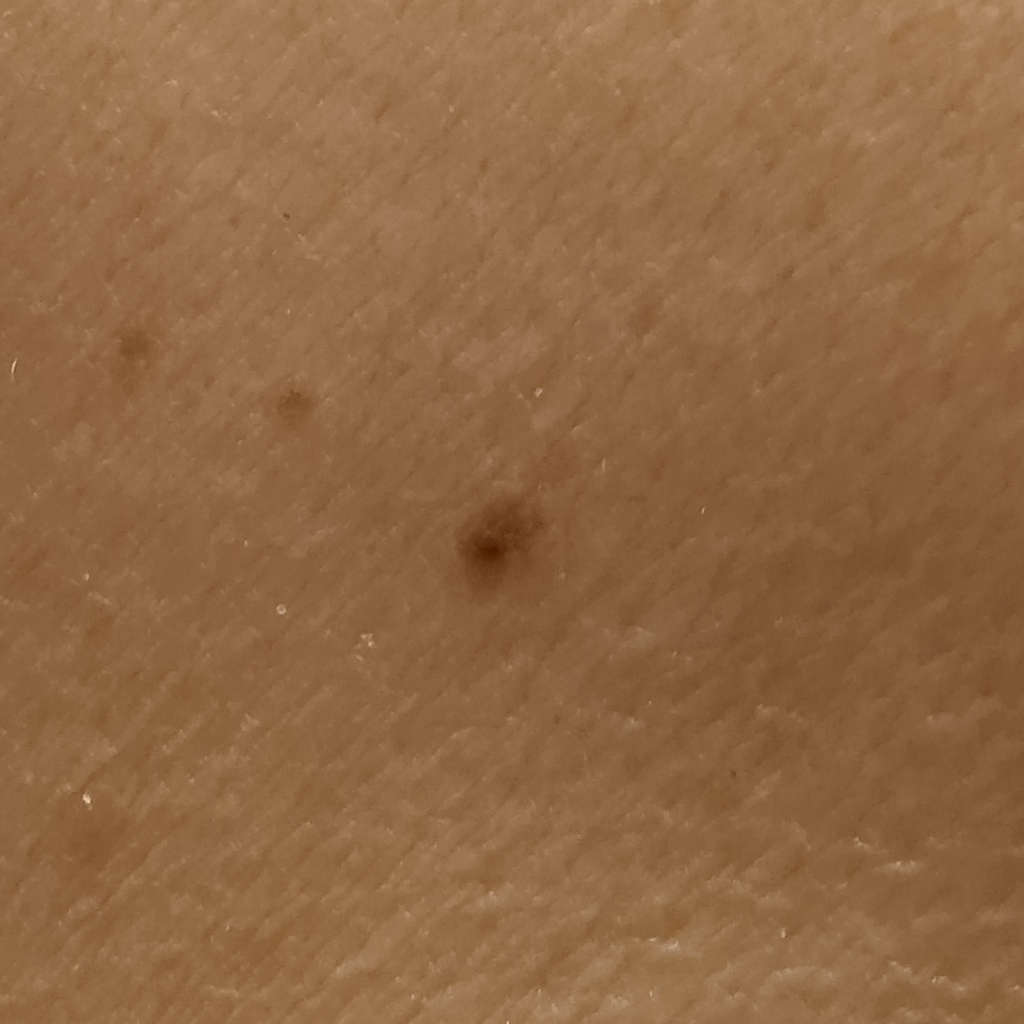Q: How does the patient's skin react to sun?
A: skin reddens painfully with sun exposure
Q: What kind of image is this?
A: clinical photograph
Q: Tell me about the patient.
A: female, age 81
Q: Why was this imaged?
A: research study (no referral diagnosis)
Q: What is the patient's nevus burden?
A: a moderate number of melanocytic nevi
Q: Where is the lesion?
A: the back
Q: What was the diagnosis?
A: melanocytic nevus (dermatologist consensus)